A dermatoscopic image of a skin lesion.
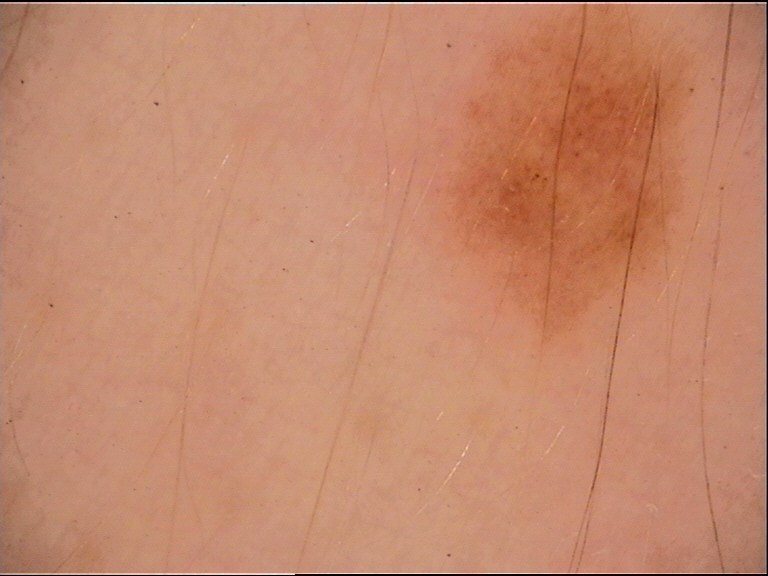Diagnosed as a benign lesion — a dysplastic junctional nevus.